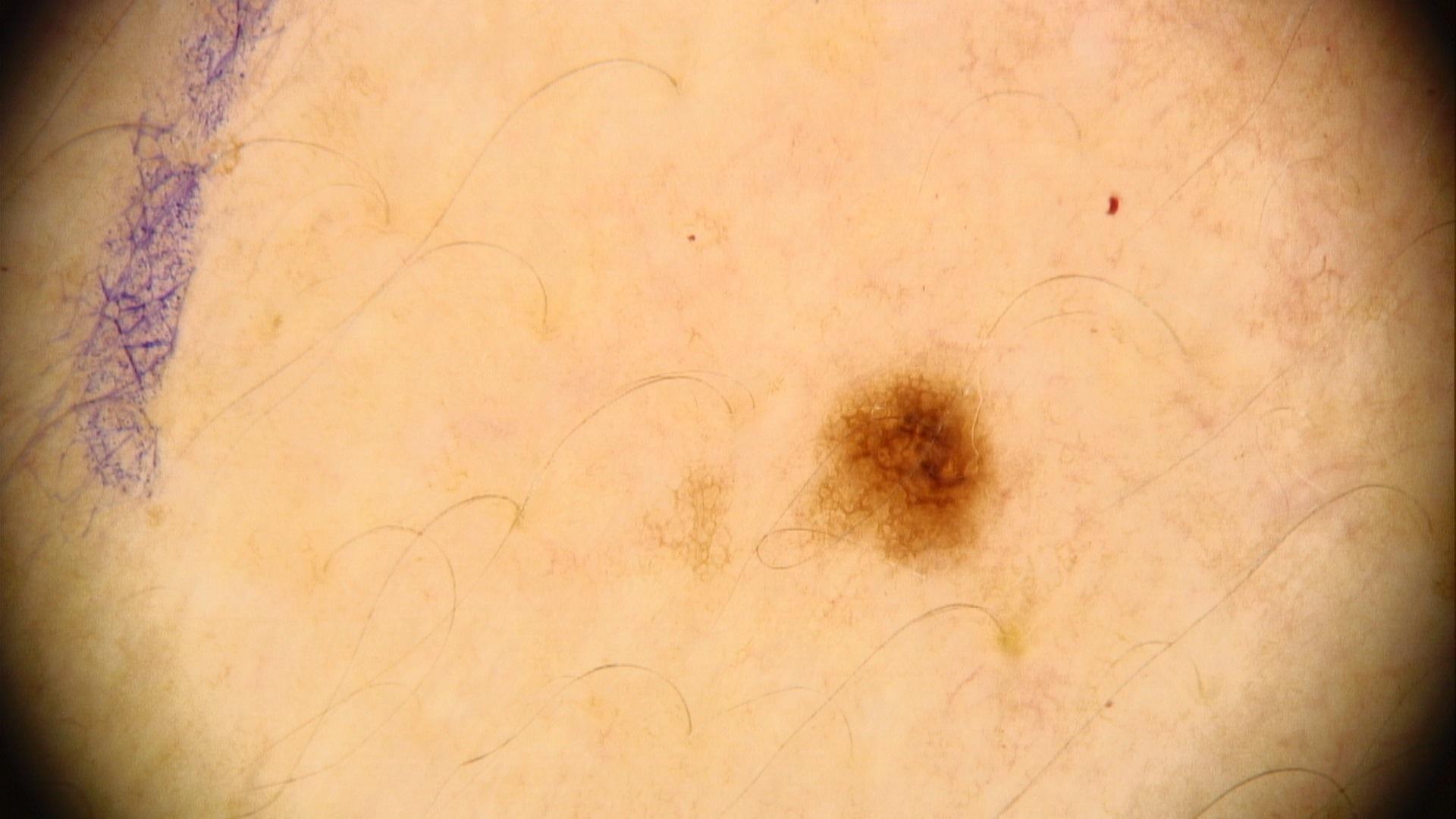Image and clinical context:
A contact-polarized dermoscopy image of a skin lesion. Recorded as skin type IV. A female subject aged approximately 55. The lesion involves the trunk, specifically the posterior trunk.
Assessment:
Consistent with a benign lesion — a nevus.